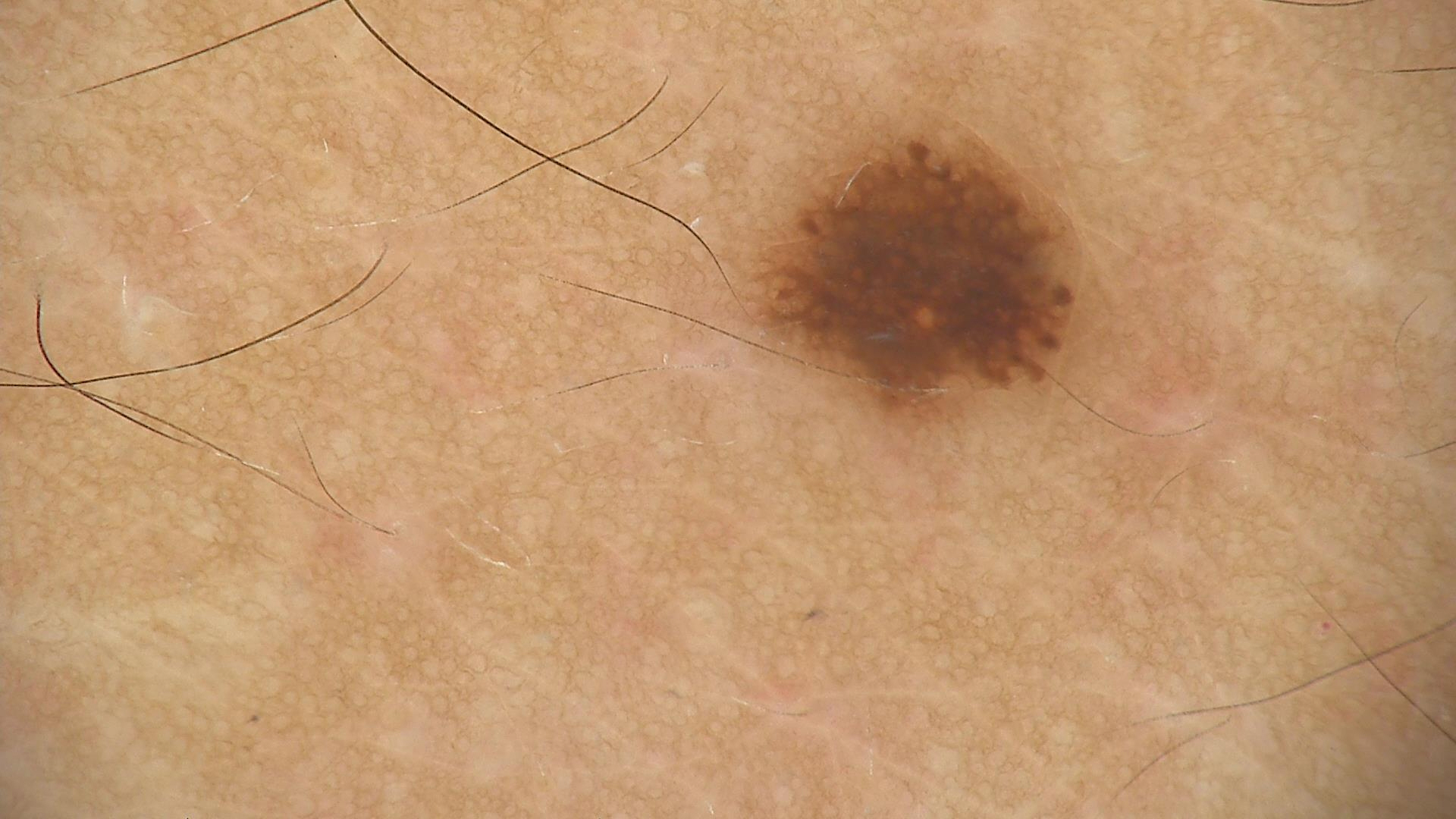image: dermatoscopy; label: dysplastic junctional nevus (expert consensus).